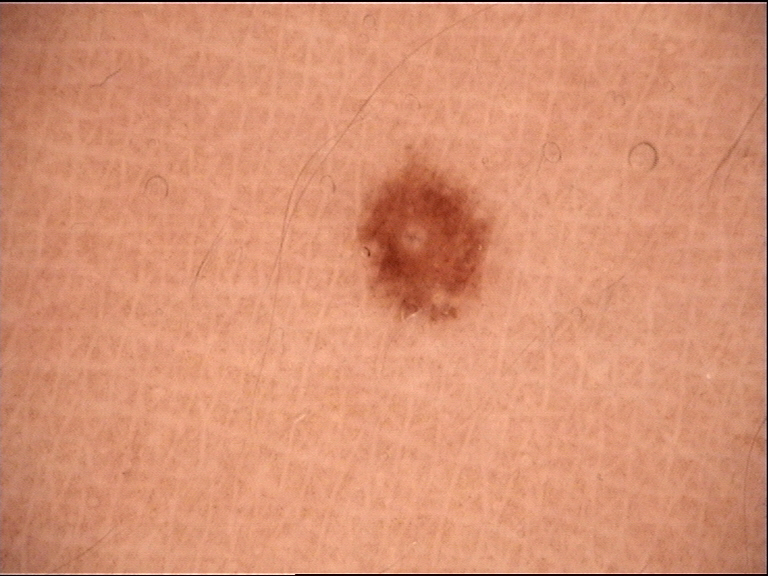The diagnostic label was a dysplastic junctional nevus.